Texture is reported as rough or flaky and raised or bumpy, skin tone: Fitzpatrick IV; human graders estimated a MST of 3, present for three to twelve months, the patient described the issue as a growth or mole, reported lesion symptoms include enlargement, the photograph was taken at an angle, the lesion involves the head or neck:
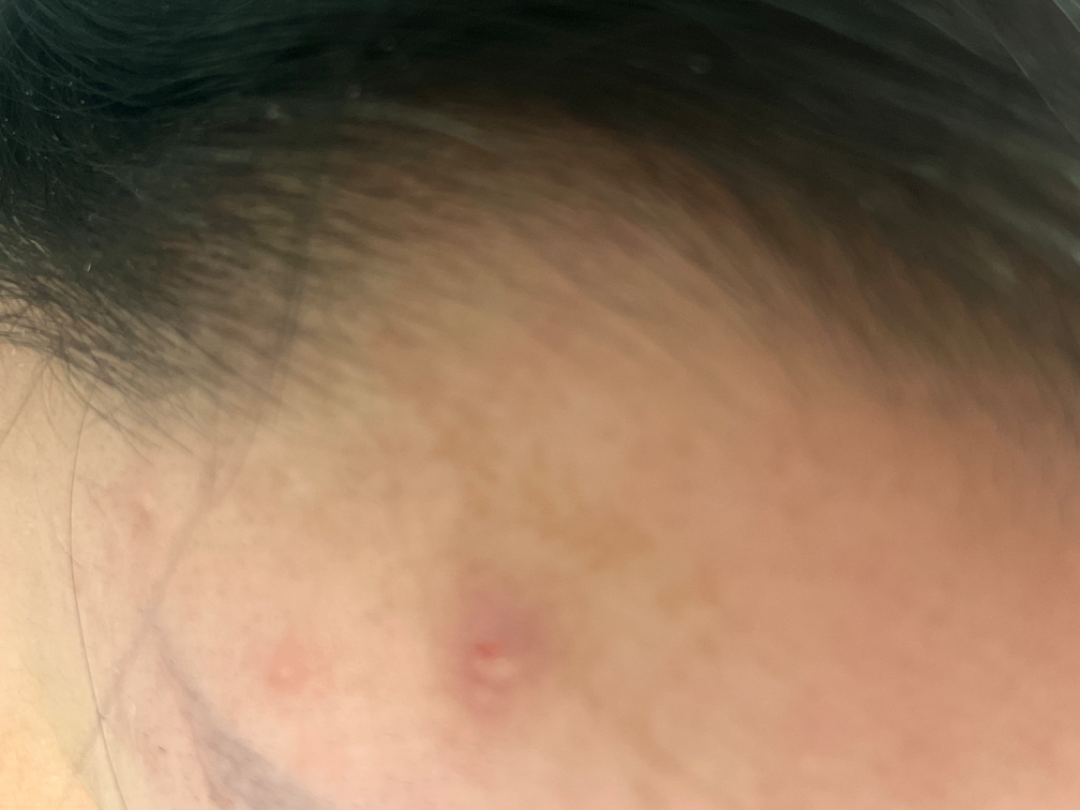The case was indeterminate on photographic review.